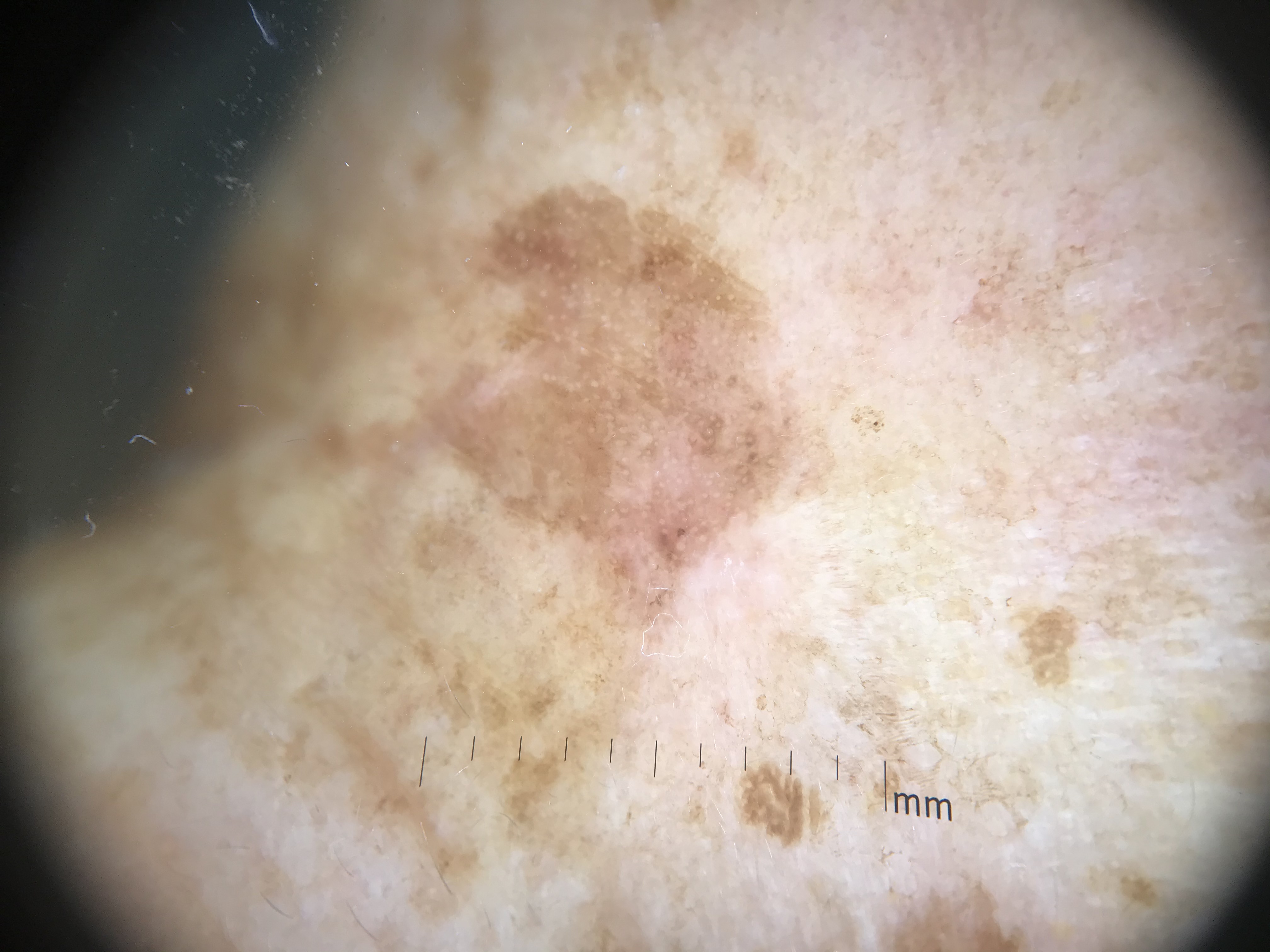Q: What is the diagnosis?
A: seborrheic keratosis (expert consensus)